Self-categorized by the patient as a rash; present for less than one week; located on the back of the hand, arm, front of the torso and head or neck; symptoms reported: itching; the lesion is described as flat; no constitutional symptoms were reported; this image was taken at an angle — 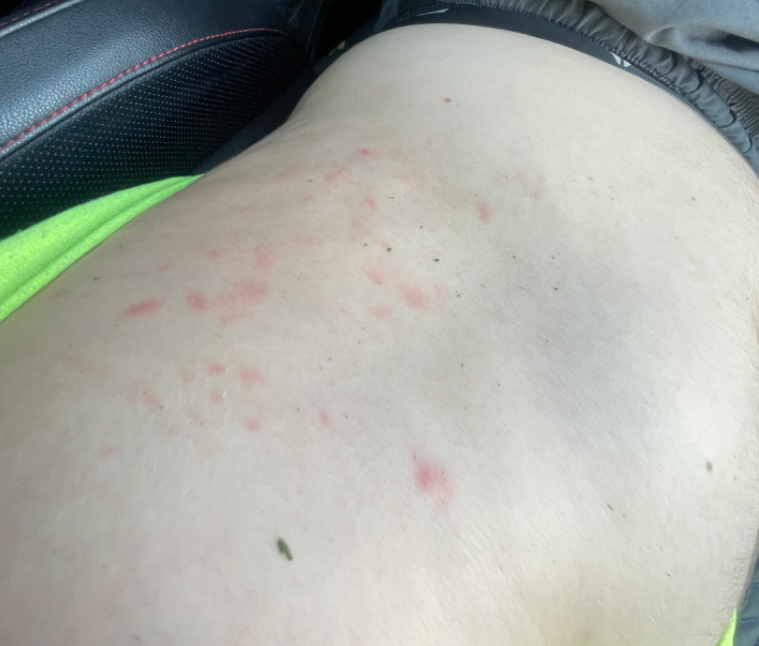{
  "differential": "Acne"
}